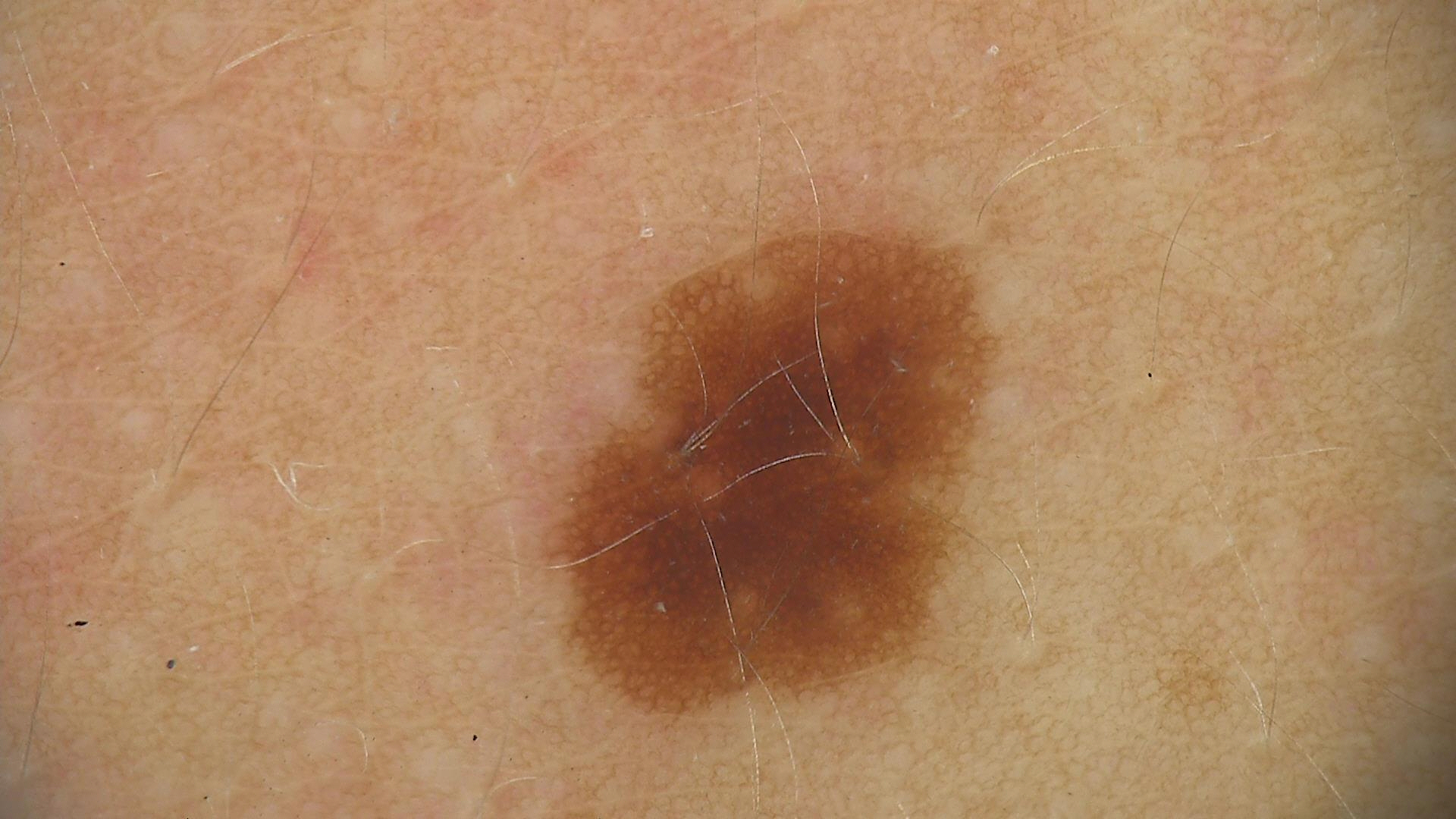modality — dermoscopy
diagnosis — dysplastic junctional nevus (expert consensus)